The patient says their skin tans without first burning; on a questionnaire the patient reported a personal history of skin cancer, a personal history of cancer, and no sunbed use; a dermoscopic image of a skin lesion; referred for assessment of suspected basal cell carcinoma; the patient describes having few moles overall; a female subject 60 years old.
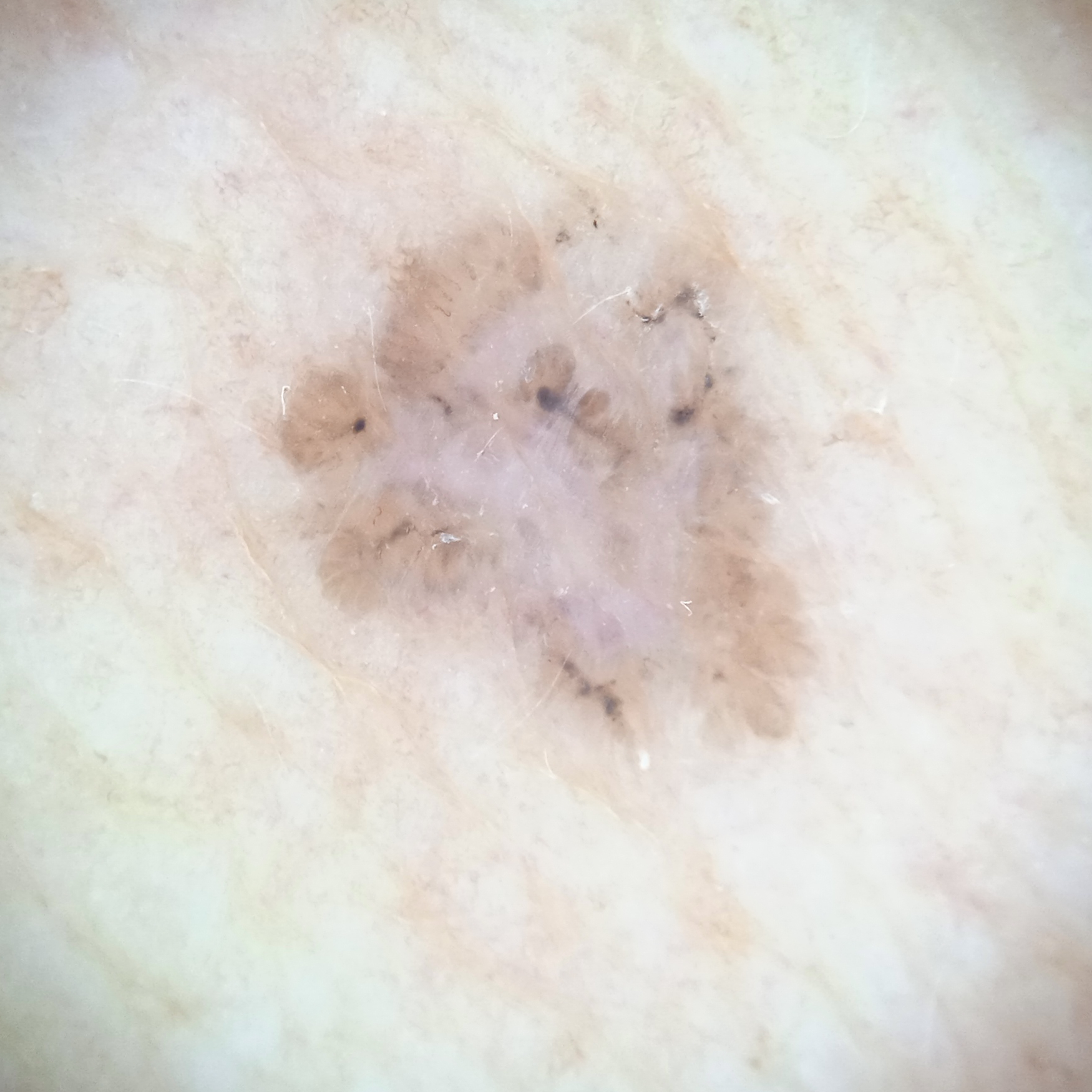anatomic site: the torso, size: 7.2 mm, diagnostic label: basal cell carcinoma (dermatologist consensus).